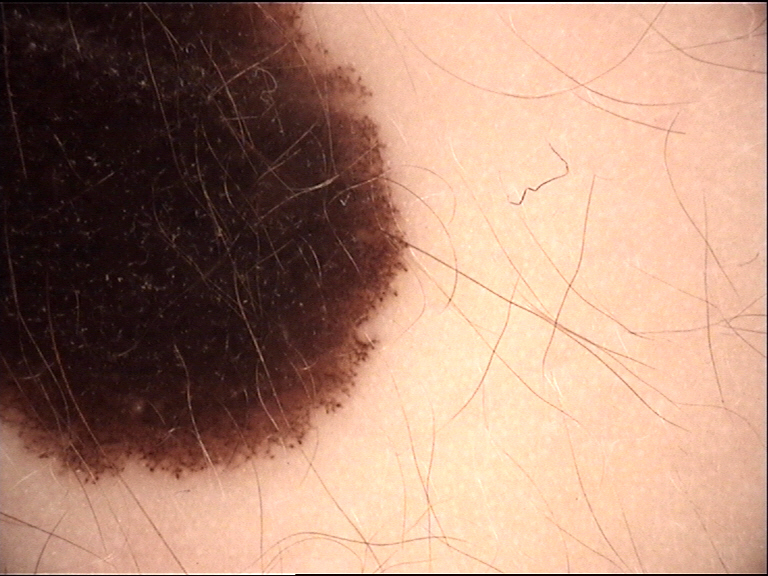<lesion>
  <diagnosis>
    <name>congenital compound nevus</name>
    <code>ccb</code>
    <malignancy>benign</malignancy>
    <super_class>melanocytic</super_class>
    <confirmation>expert consensus</confirmation>
  </diagnosis>
</lesion>